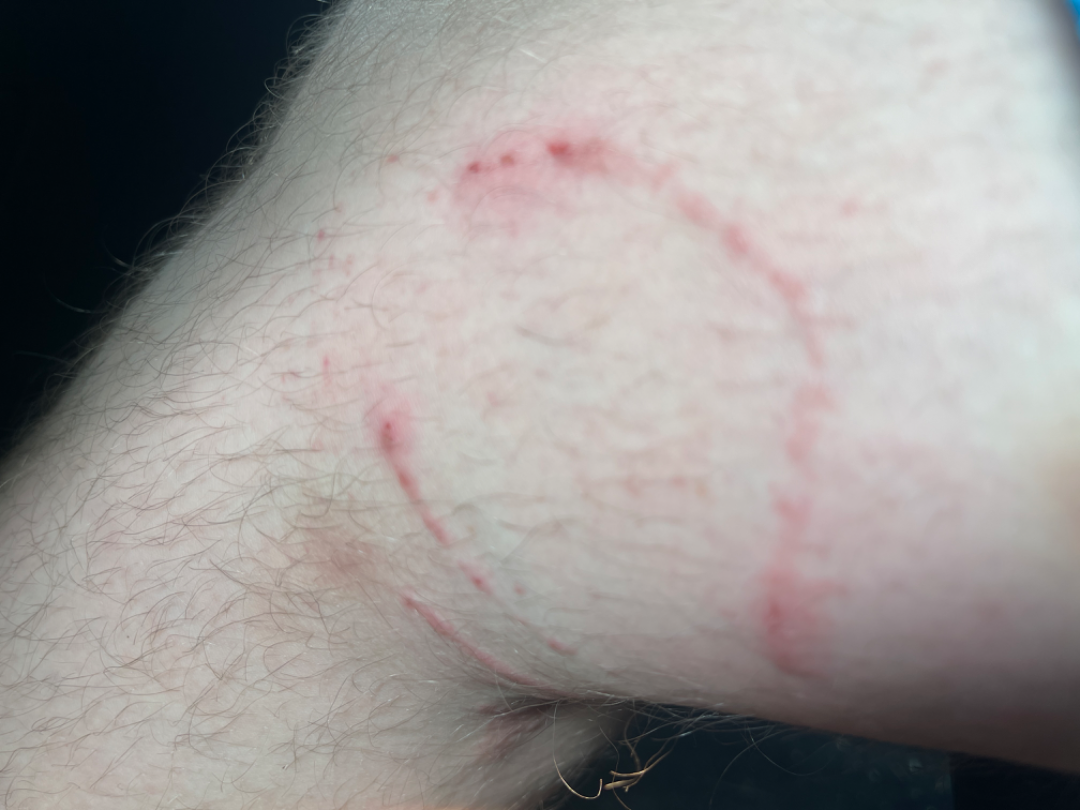History: The patient notes the condition has been present for less than one week. The lesion is described as raised or bumpy. Symptoms reported: itching. The patient considered this a rash. A close-up photograph. The patient is 18–29, male. The leg is involved. Impression: The reviewing clinician's impression was: the differential, in no particular order, includes Tinea and Erythema annulare centrifugum.